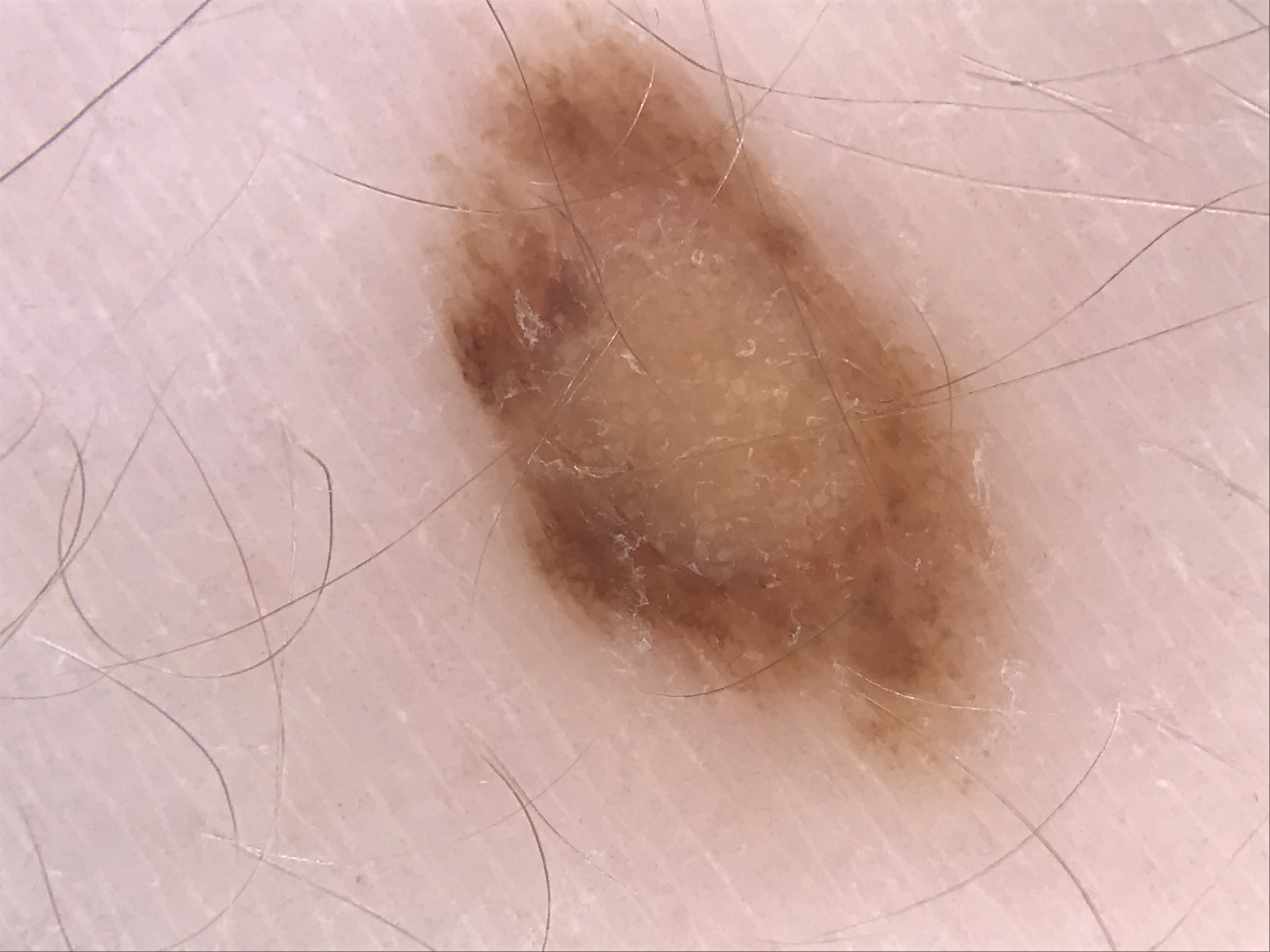<dermoscopy>
<diagnosis>
<name>dysplastic compound nevus</name>
<code>cd</code>
<malignancy>benign</malignancy>
<super_class>melanocytic</super_class>
<confirmation>expert consensus</confirmation>
</diagnosis>
</dermoscopy>